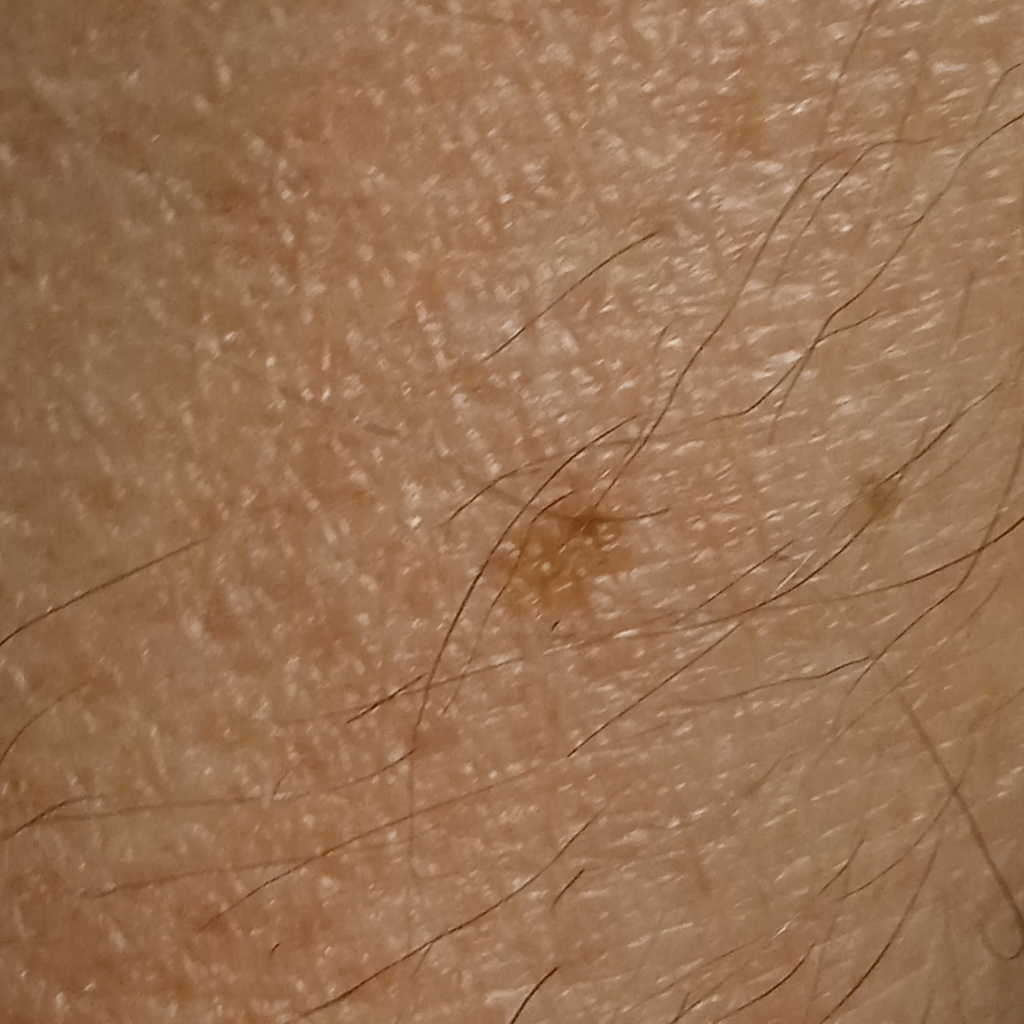{
  "sun_reaction": "skin tans without first burning",
  "mole_burden": "few melanocytic nevi overall",
  "referral": "research study (no referral diagnosis)",
  "patient": {
    "age": 79,
    "sex": "male"
  },
  "risk_factors": {
    "negative": [
      "no immunosuppression",
      "no personal history of cancer"
    ]
  },
  "image": "clinical photograph",
  "lesion_location": "an arm",
  "lesion_size": {
    "diameter_mm": 4.2
  },
  "diagnosis": {
    "name": "seborrheic keratosis",
    "malignancy": "benign"
  }
}